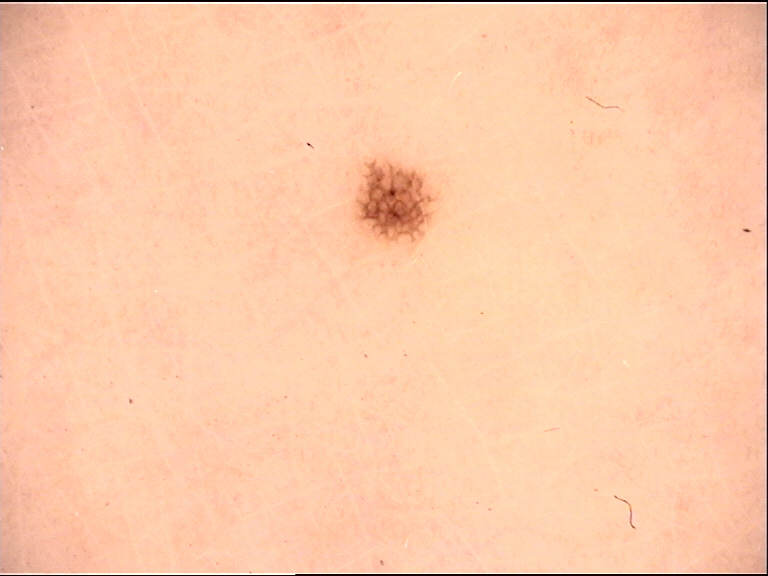Q: What kind of image is this?
A: dermatoscopy
Q: What is the diagnosis?
A: acral junctional nevus (expert consensus)